Texture is reported as raised or bumpy. The back of the hand is involved. The photo was captured at an angle. No associated systemic symptoms reported. The patient notes itching. FST V; lay reviewers estimated Monk skin tone scale 4 or 6.
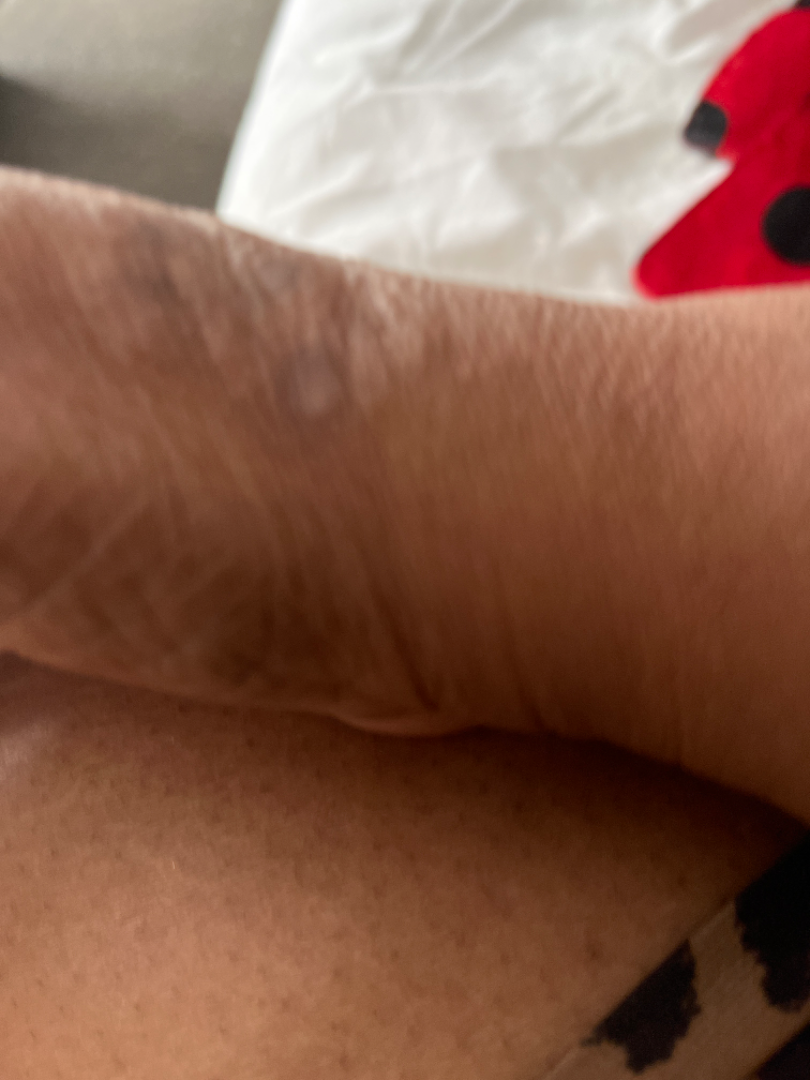Lichen Simplex Chronicus (most likely); Cutaneous sarcoidosis (considered); Tinea (remote).